The photograph was taken at an angle; the affected area is the leg:
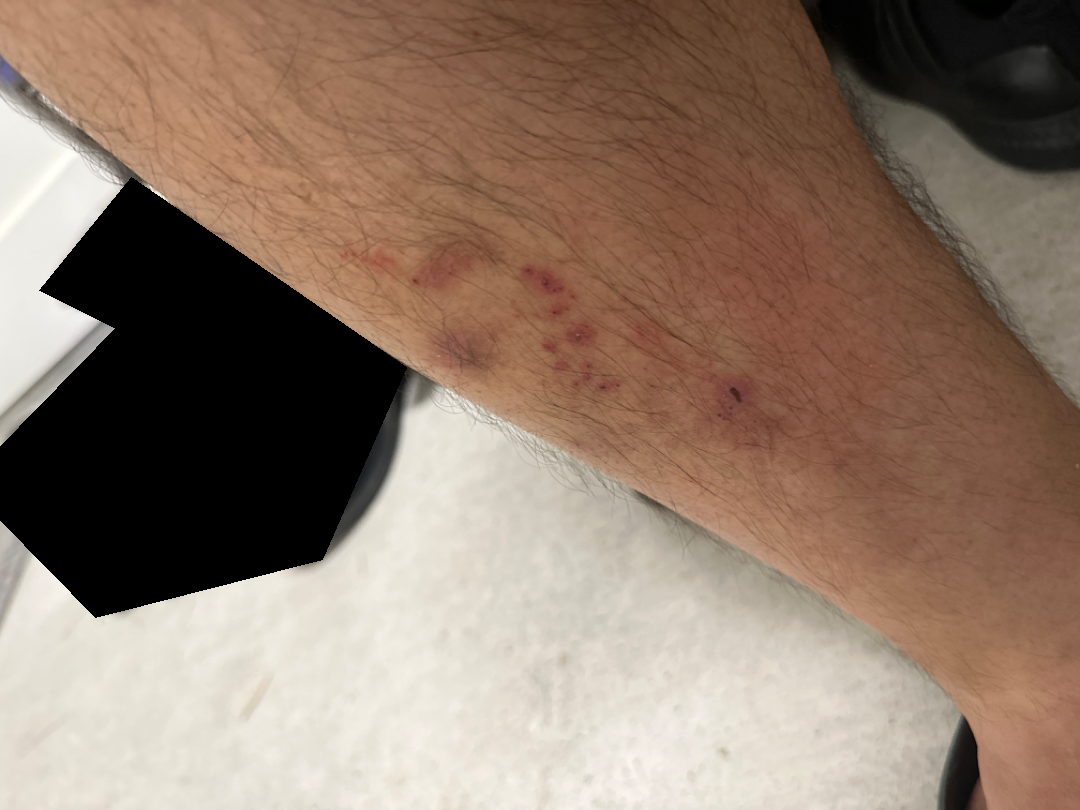No differential diagnosis could be assigned on photographic review. The patient indicates burning, bothersome appearance and itching. The patient indicates the lesion is raised or bumpy. The patient considered this skin that appeared healthy to them. FST III. Reported duration is less than one week.